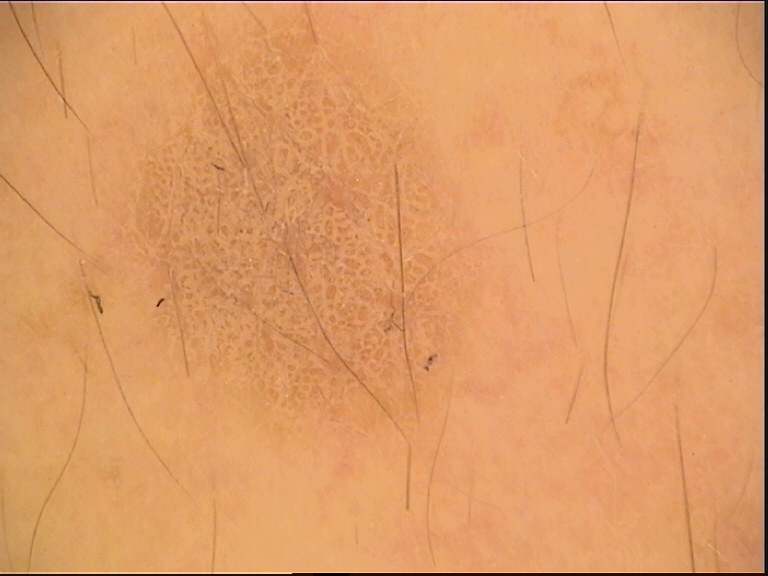Findings: The morphology is that of a keratinocytic lesion. Impression: Consistent with a benign lesion — a seborrheic keratosis.